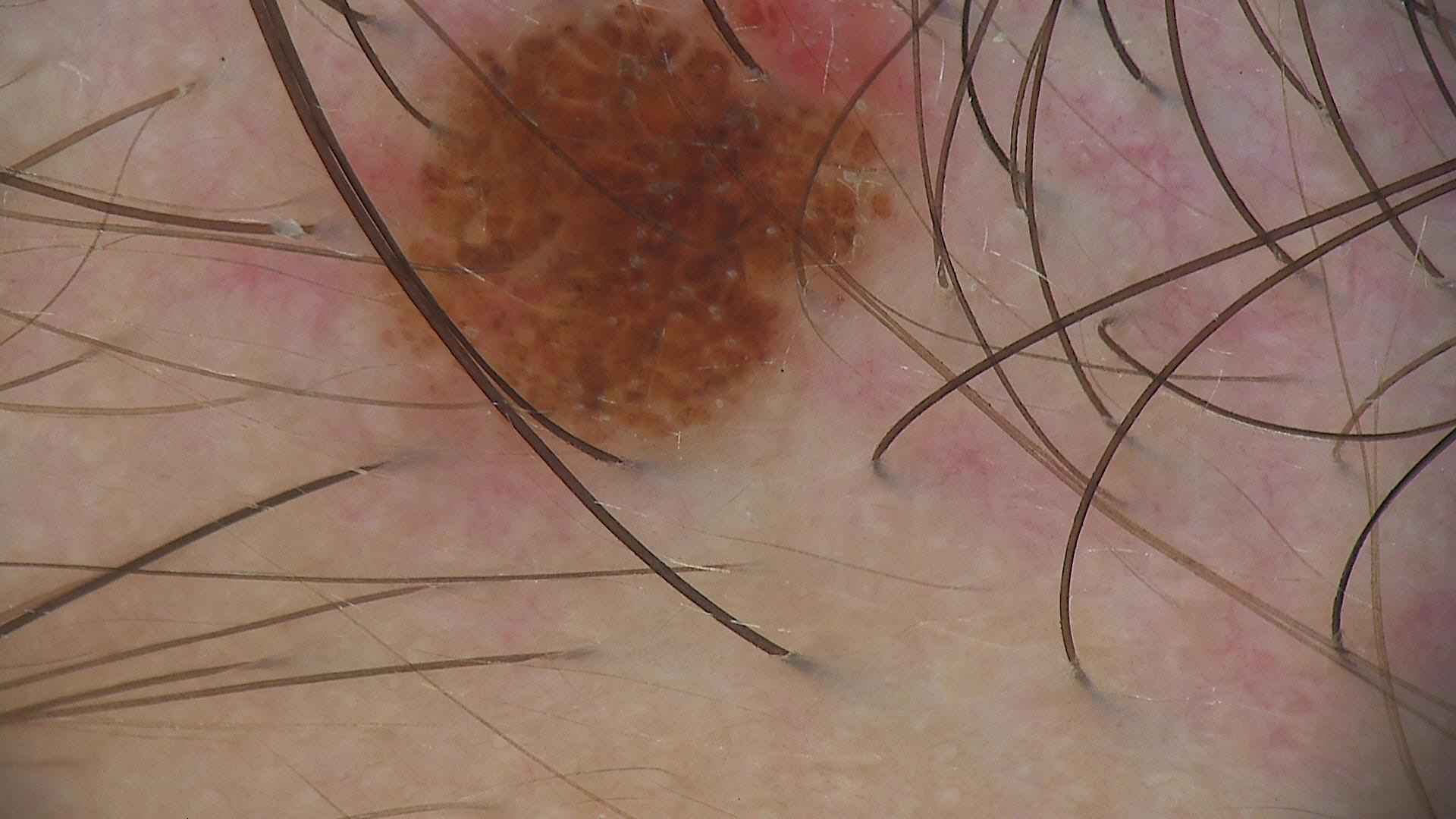Conclusion:
The diagnosis was a compound nevus.